A dermoscopic close-up of a skin lesion:
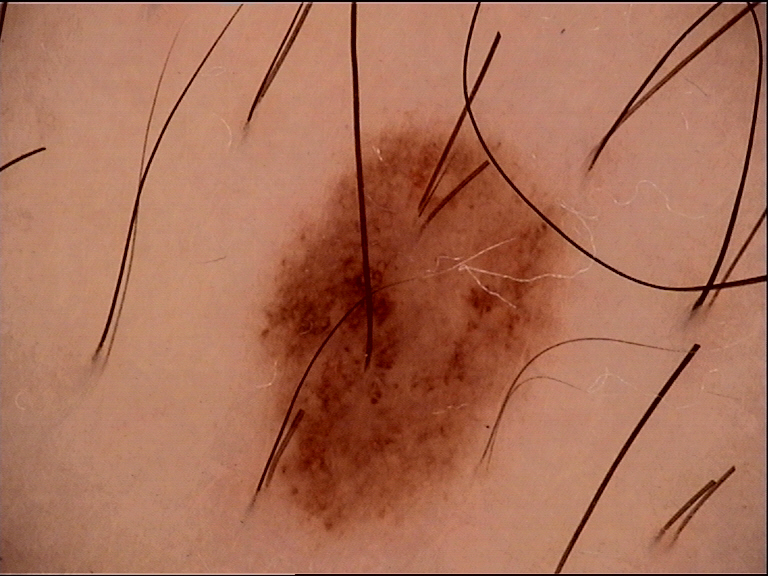  diagnosis:
    name: compound nevus
    code: cb
    malignancy: benign
    super_class: melanocytic
    confirmation: expert consensus